A female patient in their mid-50s. Dermoscopy of a skin lesion. Recorded as FST II.
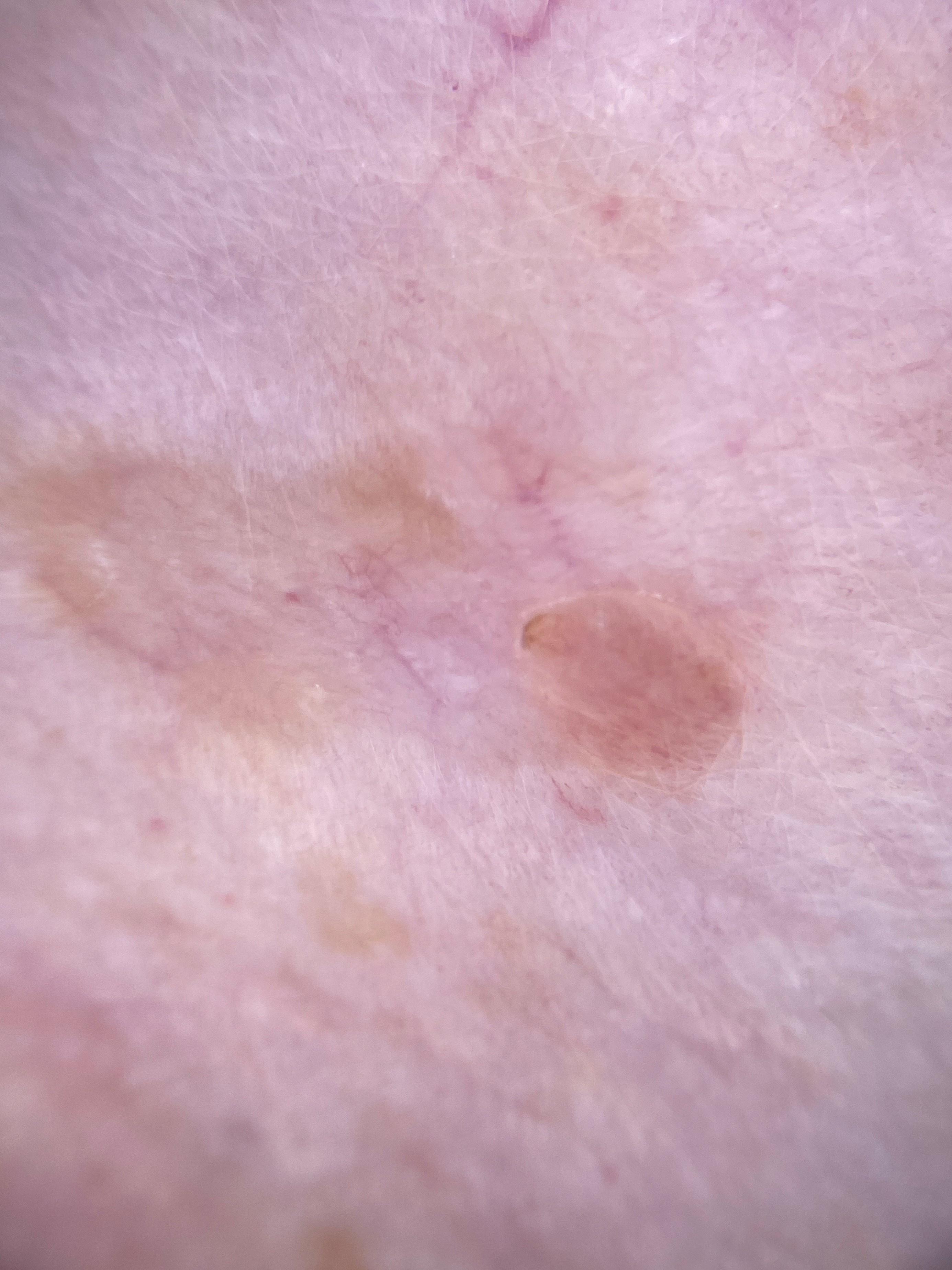diagnosis:
  name: Nevus
  malignancy: benign
  confirmation: histopathology
  lineage: melanocytic